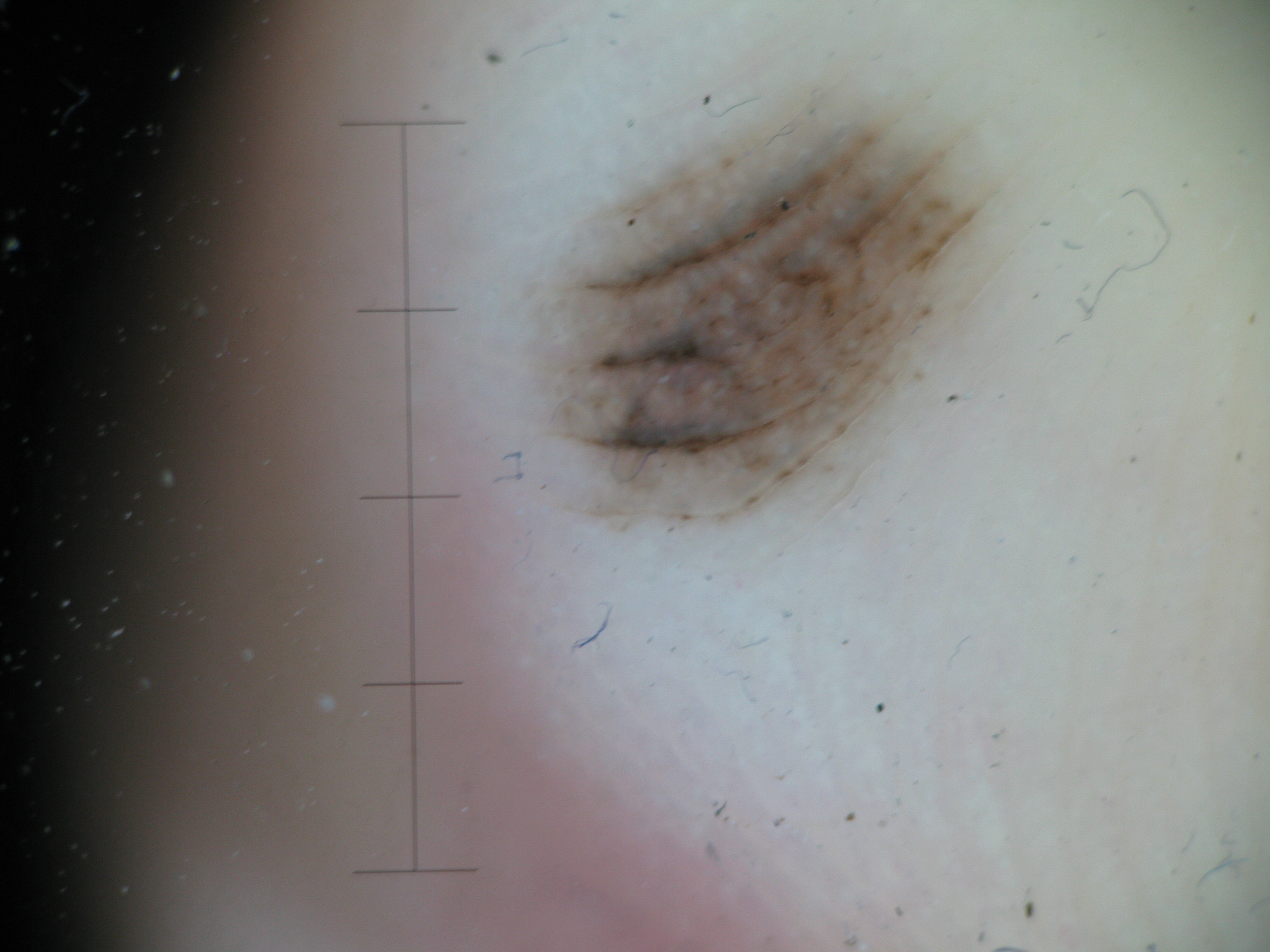The morphology is that of a banal lesion. The diagnostic label was an acral junctional nevus.